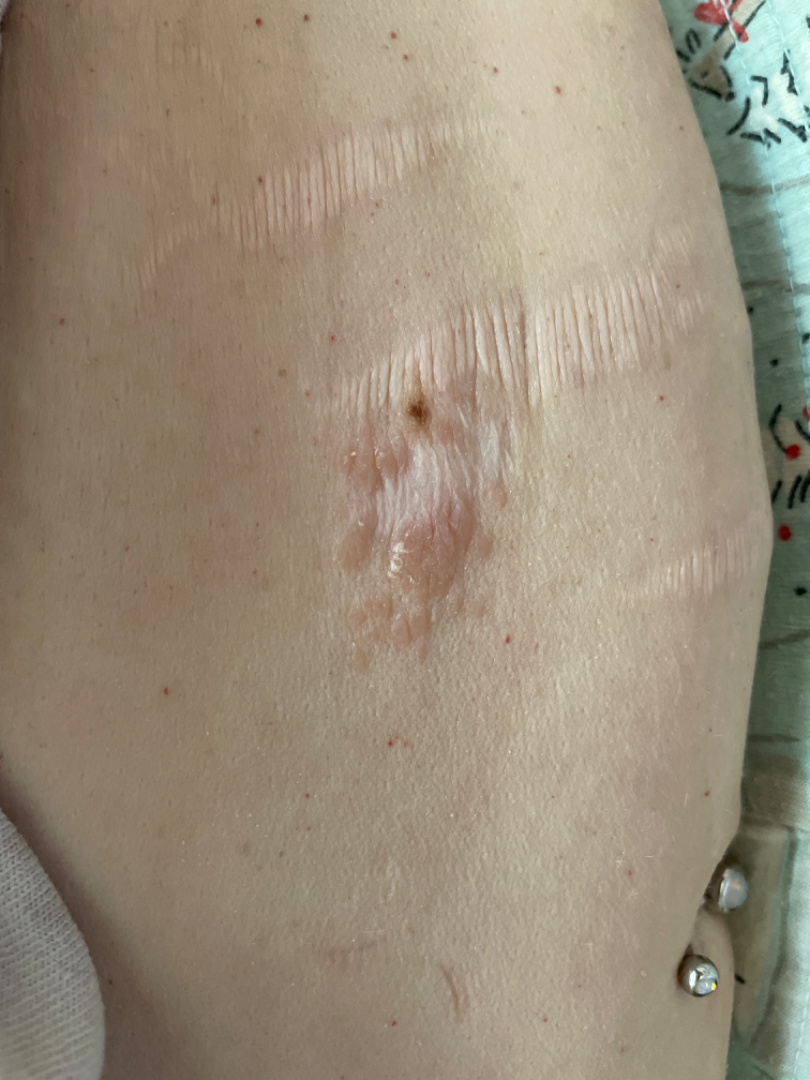assessment — not assessable
image framing — close-up
subject — female, age 40–49
body site — front of the torso